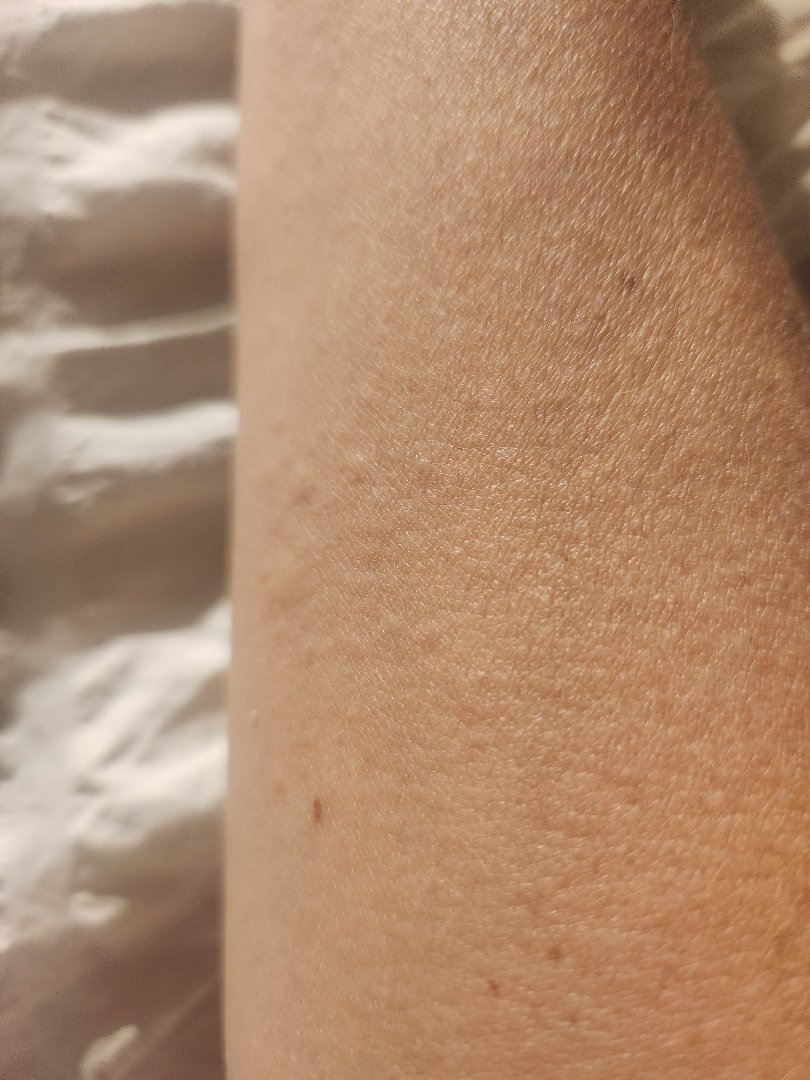Notes:
- self-categorized as · a rash
- history · one to three months
- lesion symptoms · burning, pain and itching
- image framing · at an angle
- affected area · palm, head or neck, leg, front of the torso, arm and back of the torso
- lesion texture · flat and raised or bumpy
- impression · Urticaria (leading); Eczema (lower probability)